A dermoscopic image of a skin lesion.
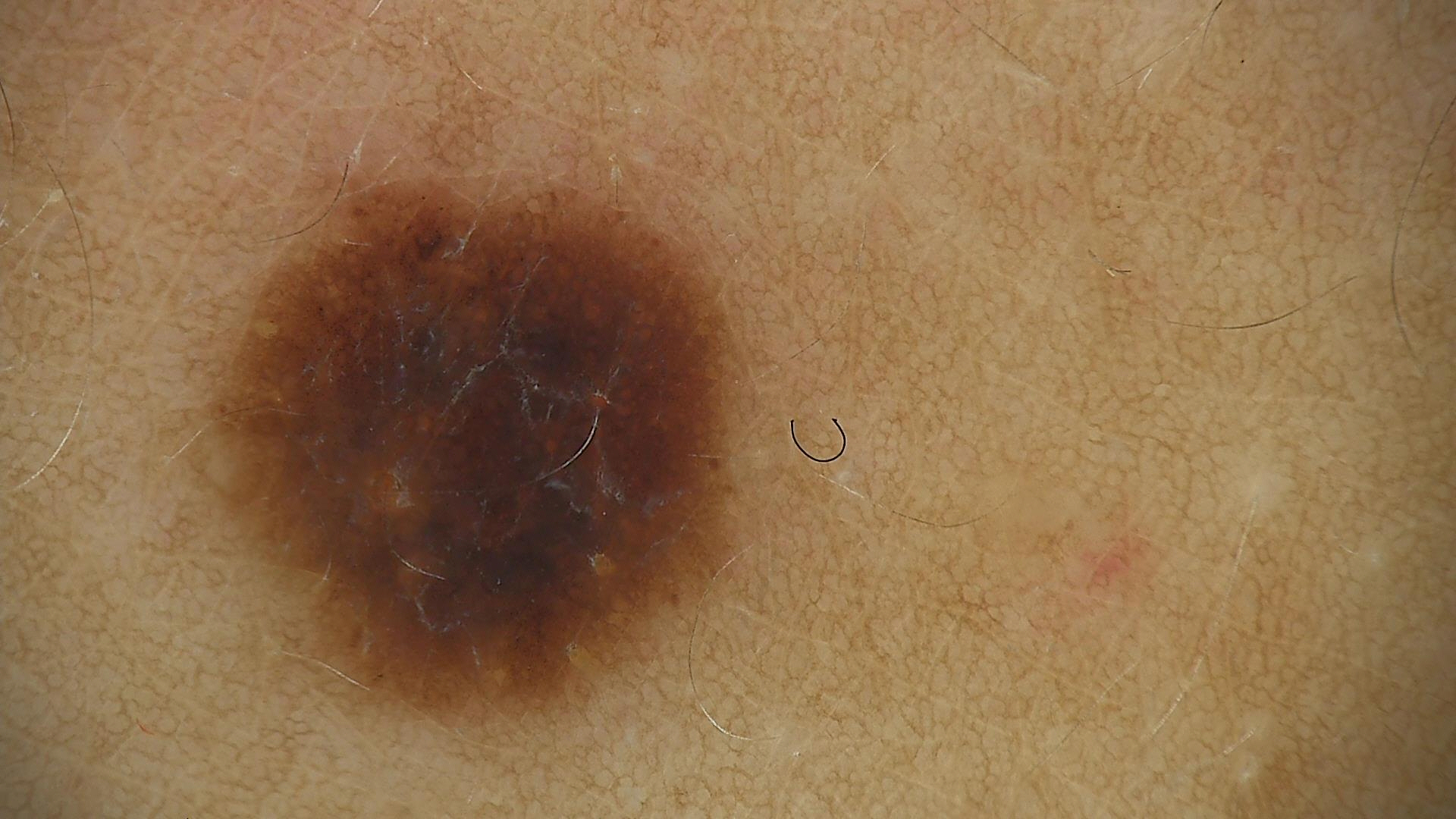Diagnosed as a dysplastic compound nevus.